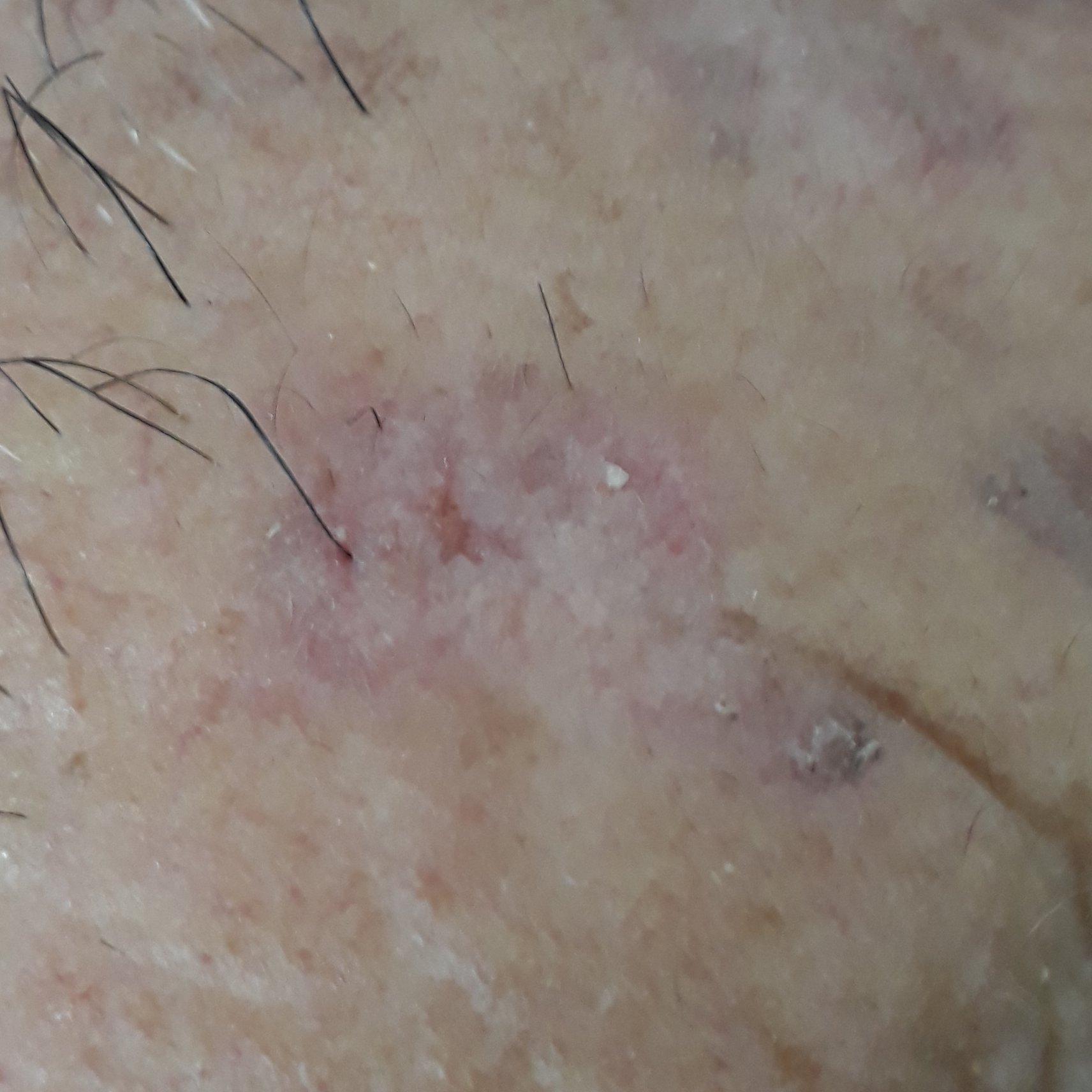| key | value |
|---|---|
| subject | male, in their 60s |
| image | smartphone clinical photo |
| skin type | IV |
| body site | the face |
| diagnostic label | actinic keratosis (biopsy-proven) |